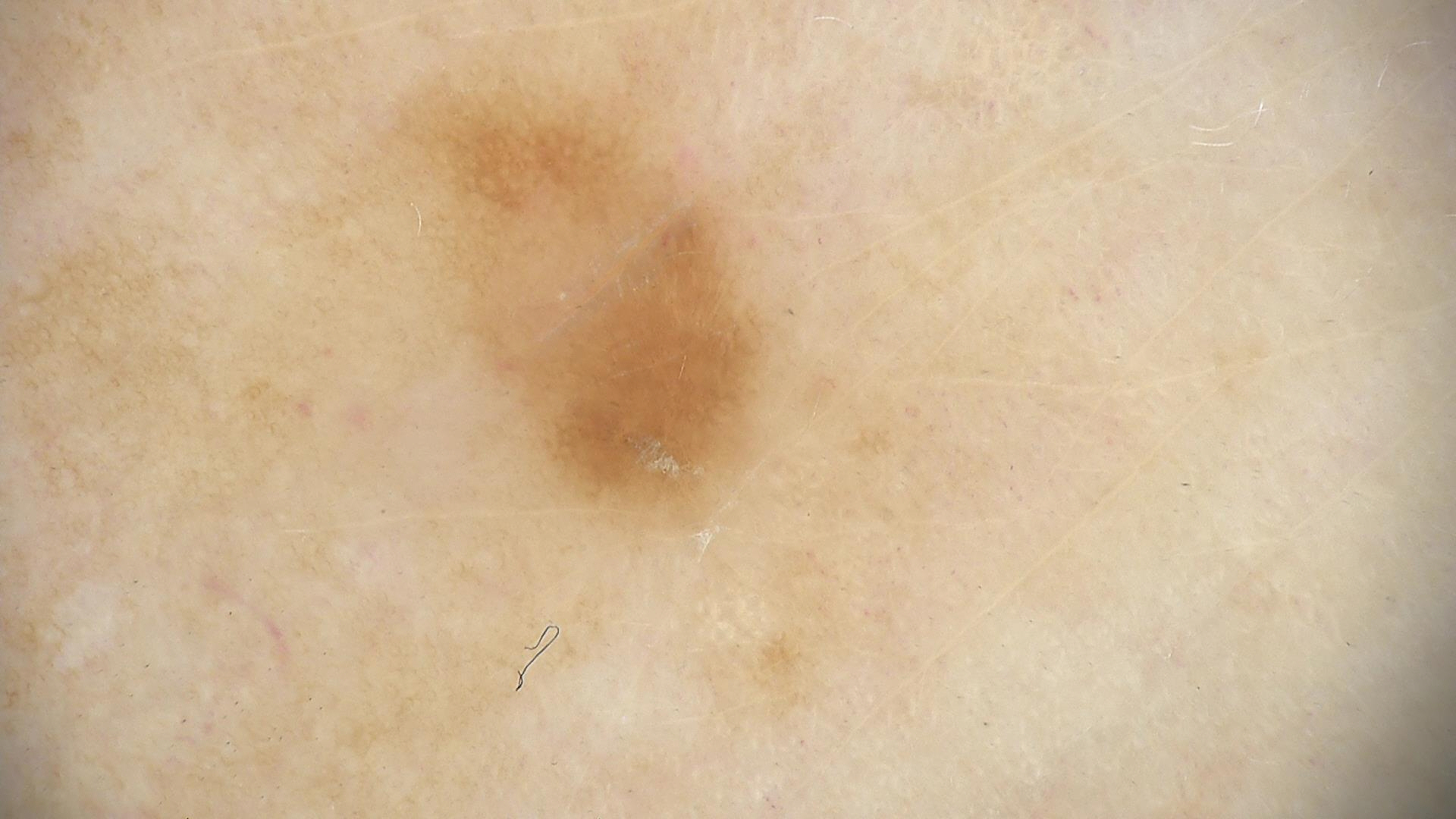Case:
A dermoscopic close-up of a skin lesion.
Conclusion:
Labeled as a dysplastic junctional nevus.